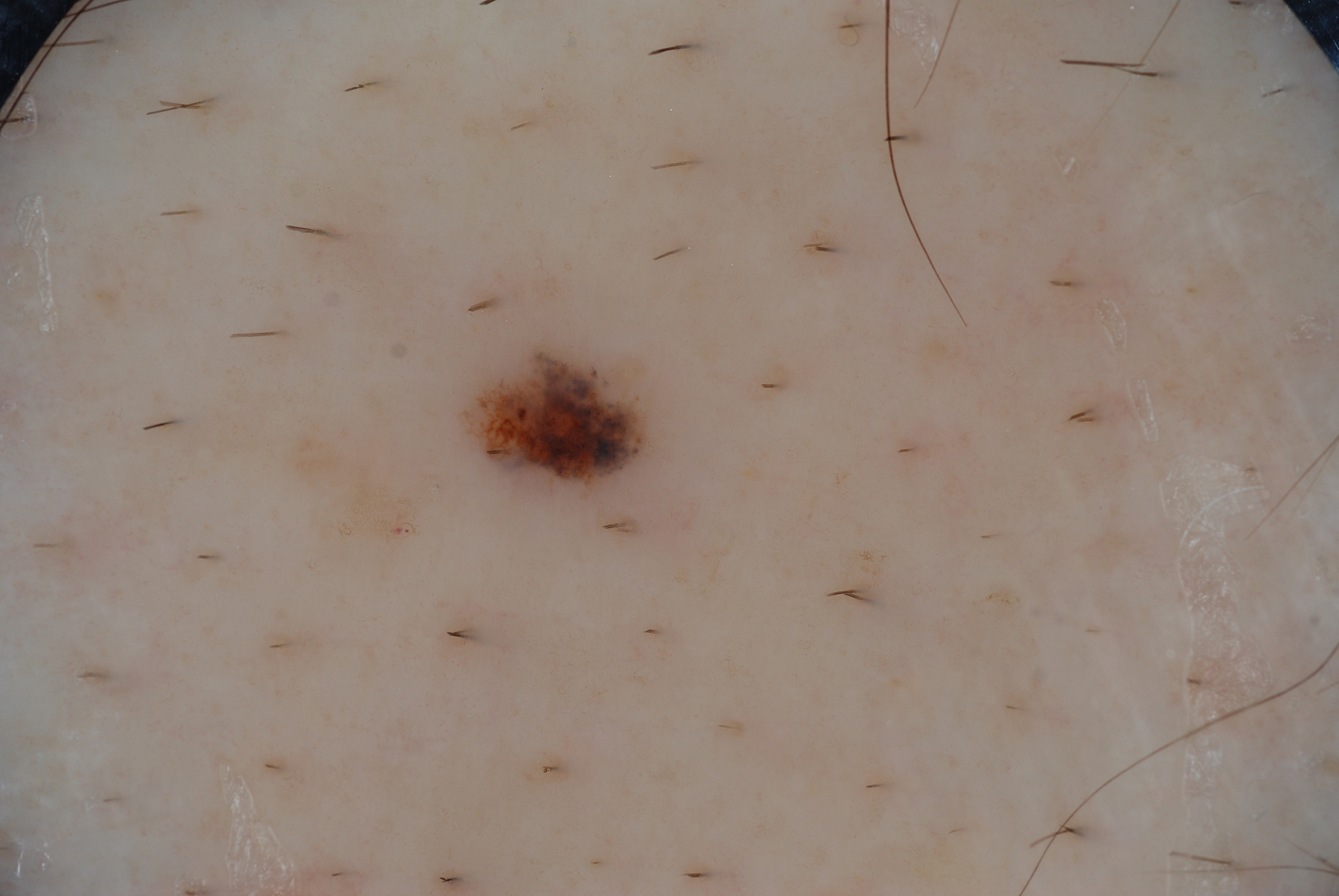image = dermoscopy of a skin lesion
patient = male, aged 73-77
bounding box = 471/343/659/497
dermoscopic findings = pigment network; absent: milia-like cysts, streaks, and negative network
lesion size = small
assessment = a melanocytic nevus